The contributor reports the lesion is raised or bumpy. The patient is 60–69, female. Present for three to twelve months. Reported lesion symptoms include itching. Self-categorized by the patient as a rash. The affected area is the front of the torso, palm, head or neck and arm. This is a close-up image — 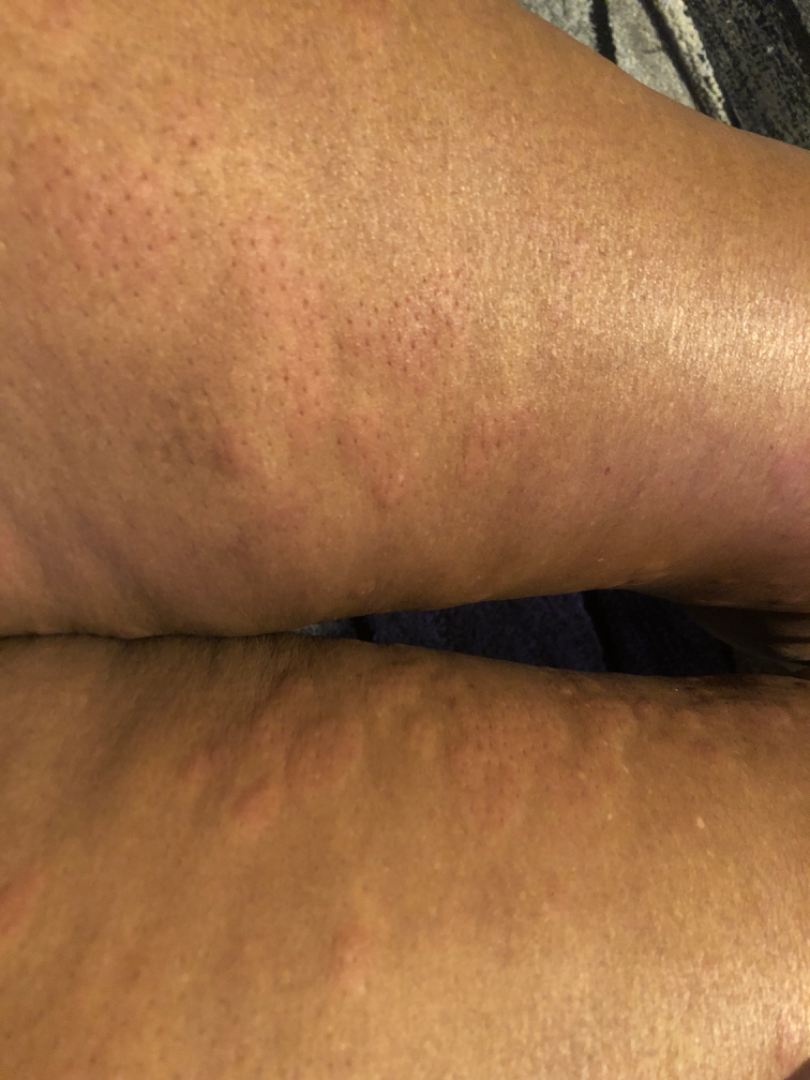clinical impression: the differential includes Urticaria and Leukocytoclastic Vasculitis, with no clear leading consideration; less probable is Drug Rash.